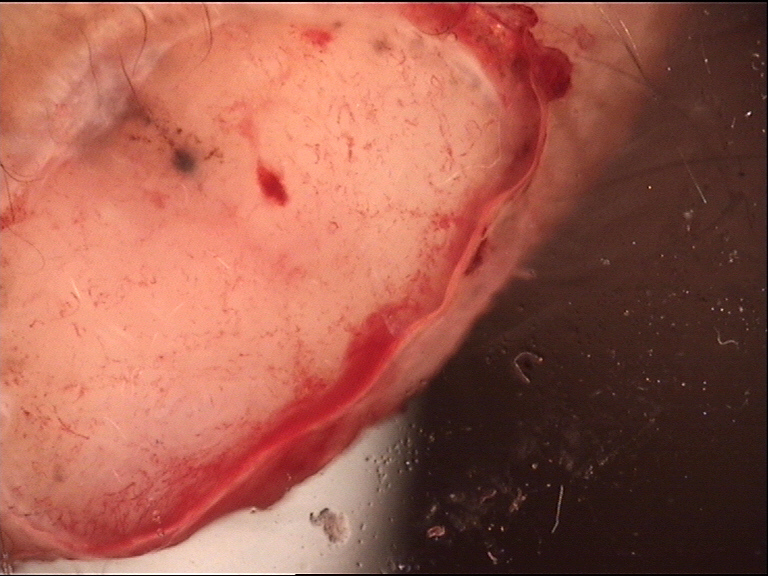lesion type = keratinocytic; label = basal cell carcinoma (biopsy-proven).